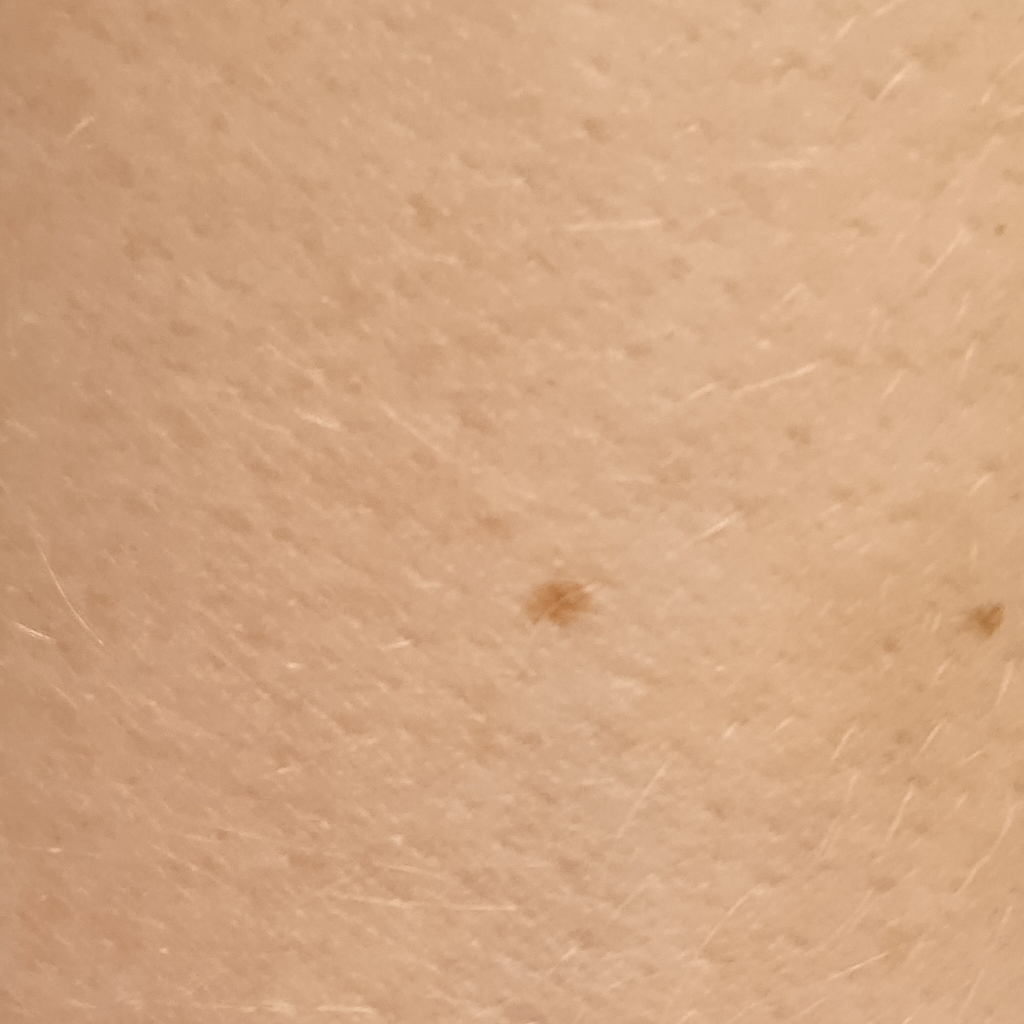Clinical context:
On a questionnaire the patient reported no sunbed use. The patient says their skin reddens painfully with sun exposure. The patient describes having a moderate number of moles. Imaged for a research study, with no referral diagnosis recorded. A female patient 50 years old.
Conclusion:
The diagnostic impression was a melanocytic nevus.